Close-up view: 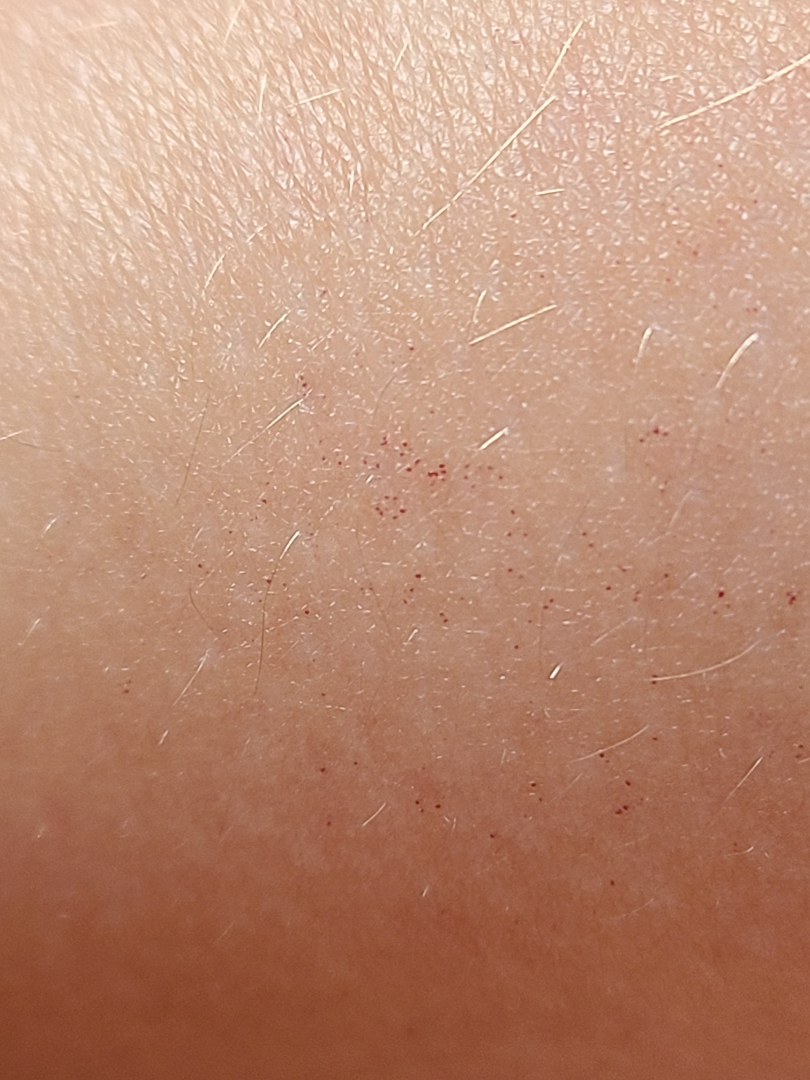On remote dermatologist review: petechiae (primary).